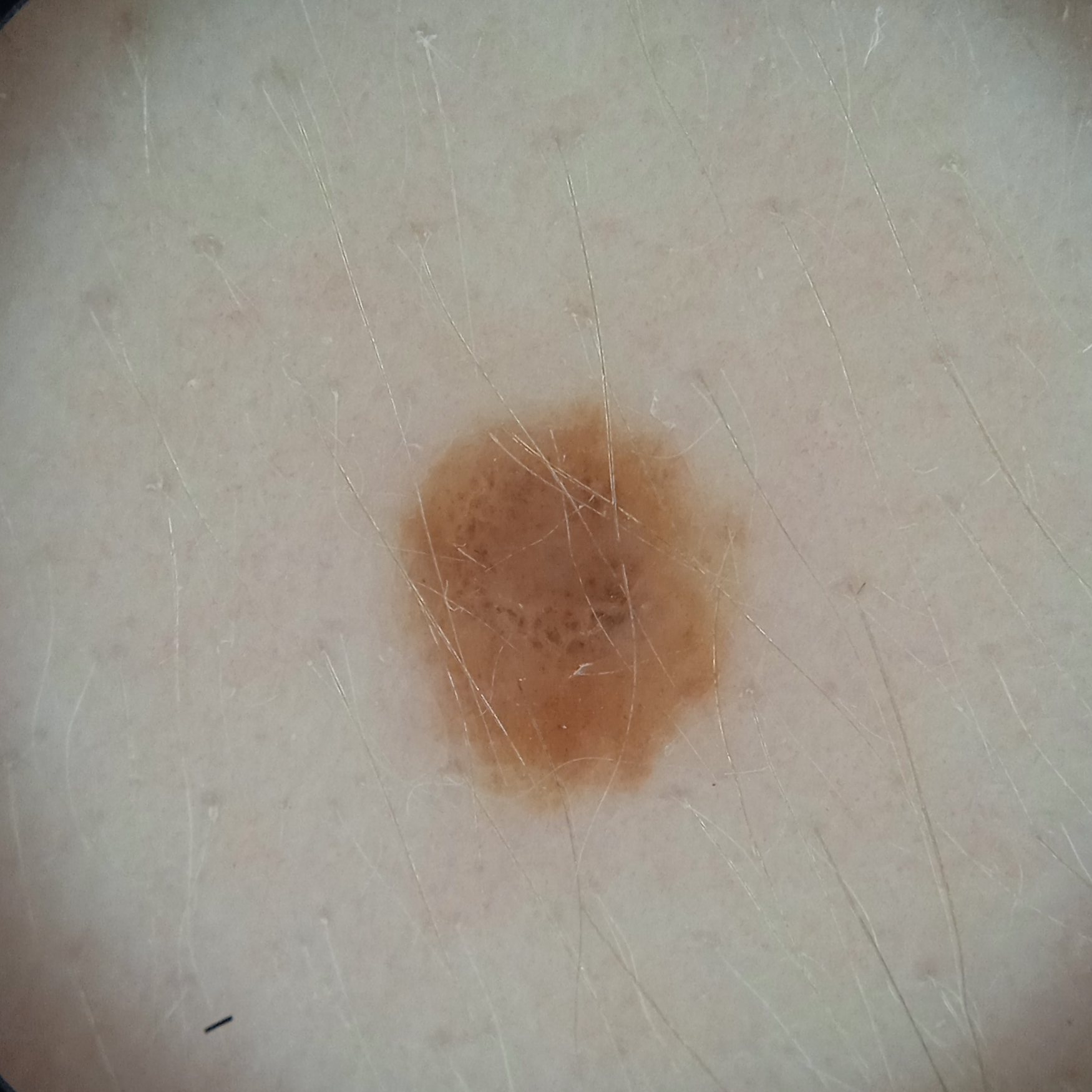  sun_reaction: skin reddens with sun exposure
  referral: research study (no referral diagnosis)
  mole_burden: a moderate number of melanocytic nevi
  image: dermoscopy
  patient:
    age: 27
    sex: female
  lesion_location: the torso
  lesion_size:
    diameter_mm: 4.4
  diagnosis:
    name: melanocytic nevus
    malignancy: benign
    unanimous: true
    certainty: good